A dermatoscopic image of a skin lesion. The subject is a male aged 13 to 17:
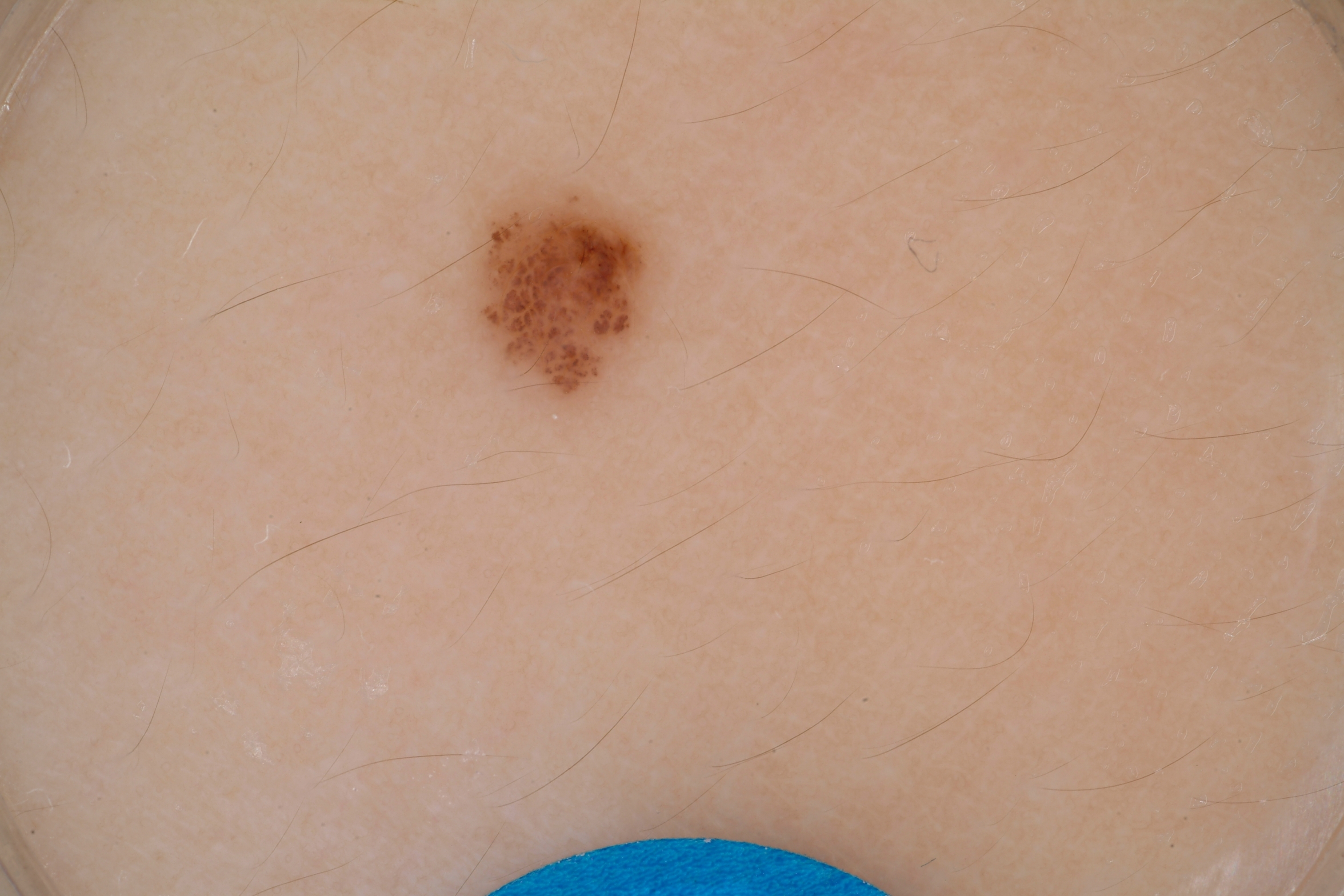Image and clinical context:
The lesion is small relative to the field of view. Dermoscopic assessment notes no milia-like cysts, negative network, streaks, or pigment network. In (x1, y1, x2, y2) order, the visible lesion spans [477, 191, 655, 402].
Conclusion:
Expert review diagnosed this as a melanocytic nevus, a benign skin lesion.